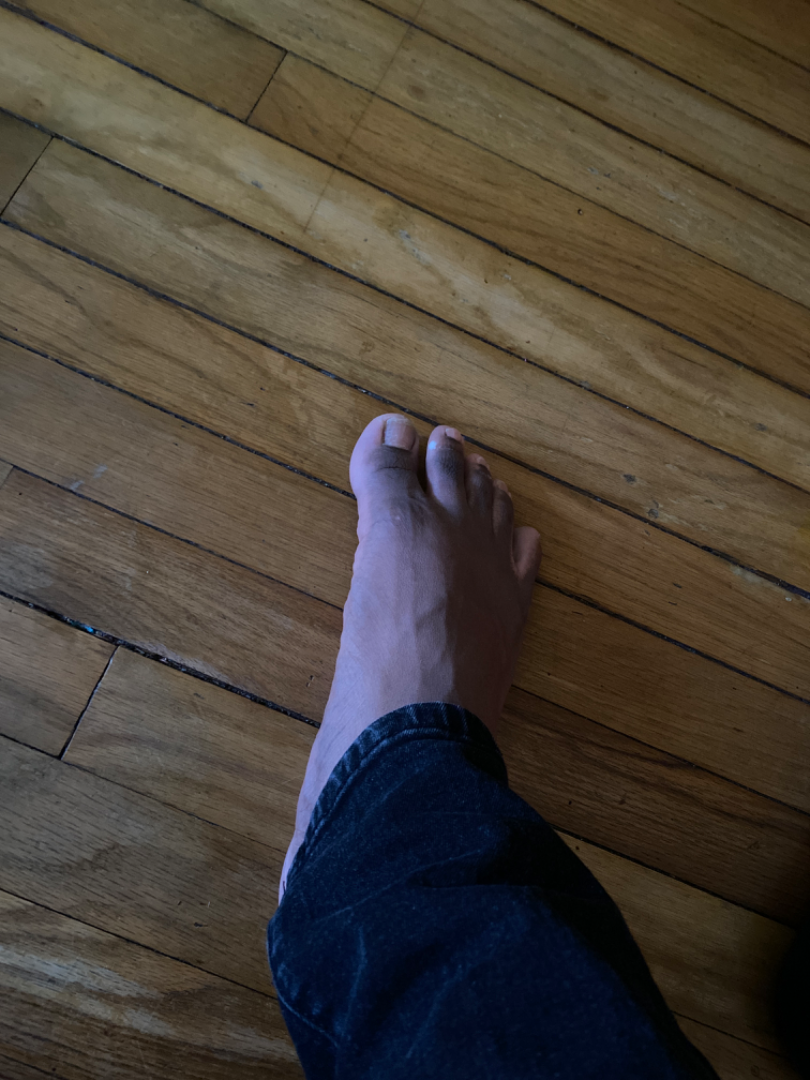<dermatology_case>
  <body_site>top or side of the foot</body_site>
  <patient>male, age 18–29</patient>
  <shot_type>at a distance</shot_type>
</dermatology_case>